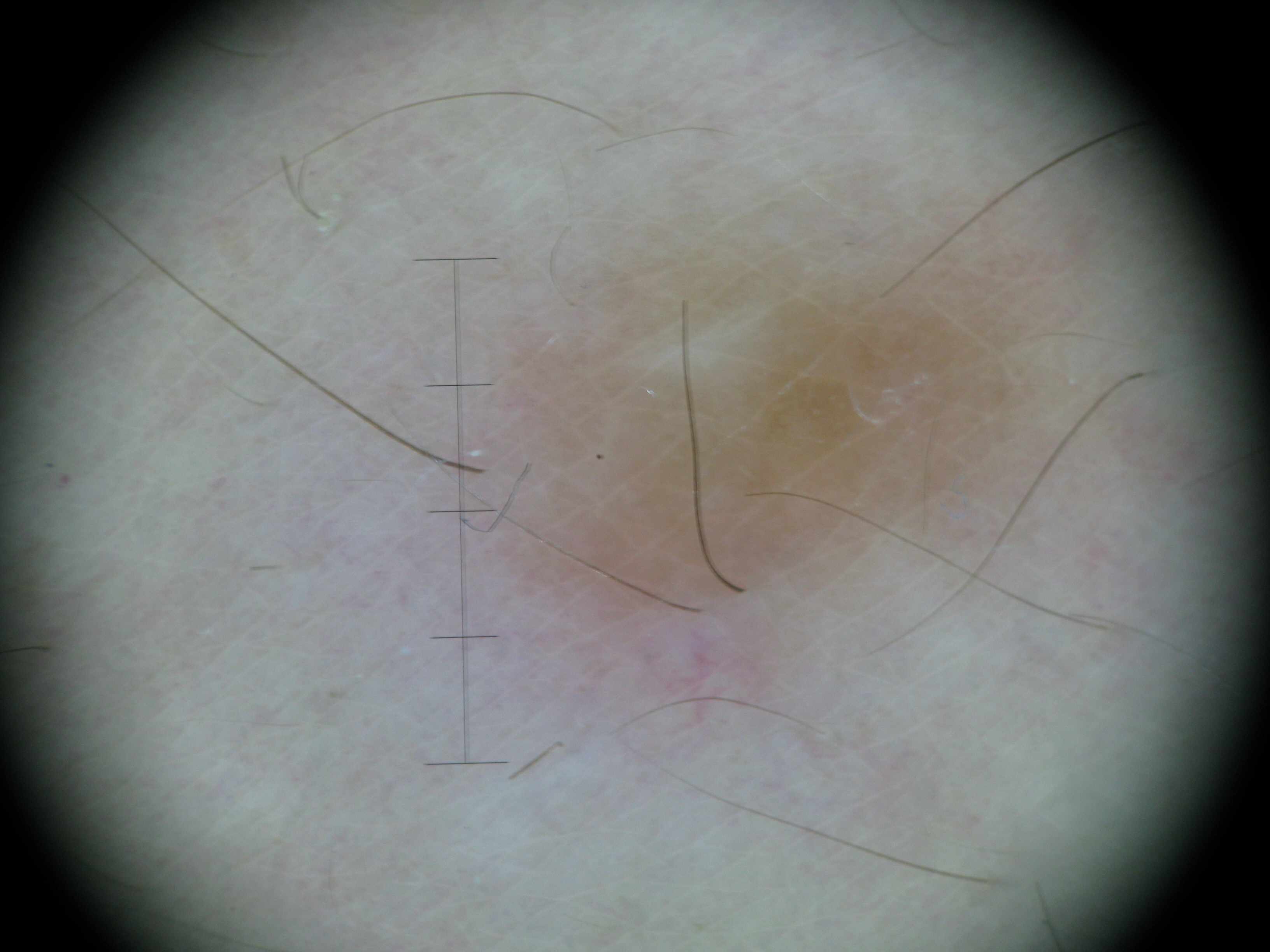<lesion>
  <image>dermoscopy</image>
  <diagnosis>
    <name>dermatofibroma</name>
    <code>df</code>
    <malignancy>benign</malignancy>
    <super_class>non-melanocytic</super_class>
    <confirmation>expert consensus</confirmation>
  </diagnosis>
</lesion>